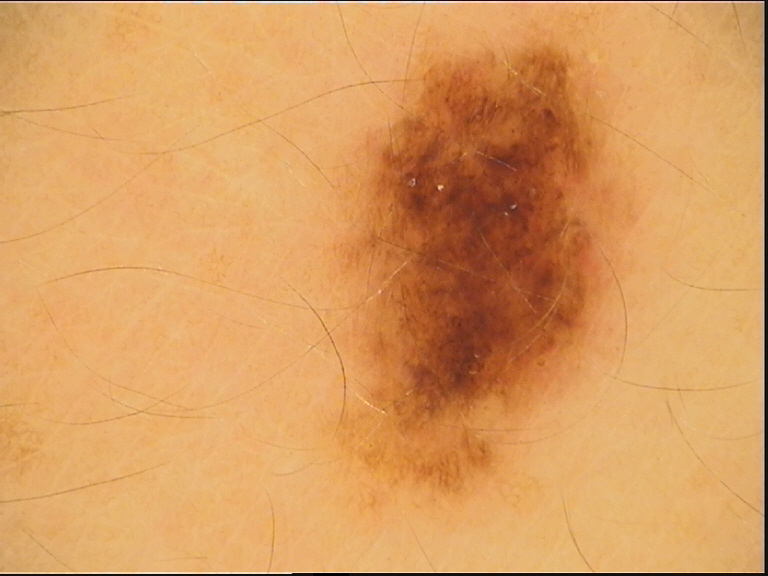Case:
– label · dysplastic junctional nevus (expert consensus)